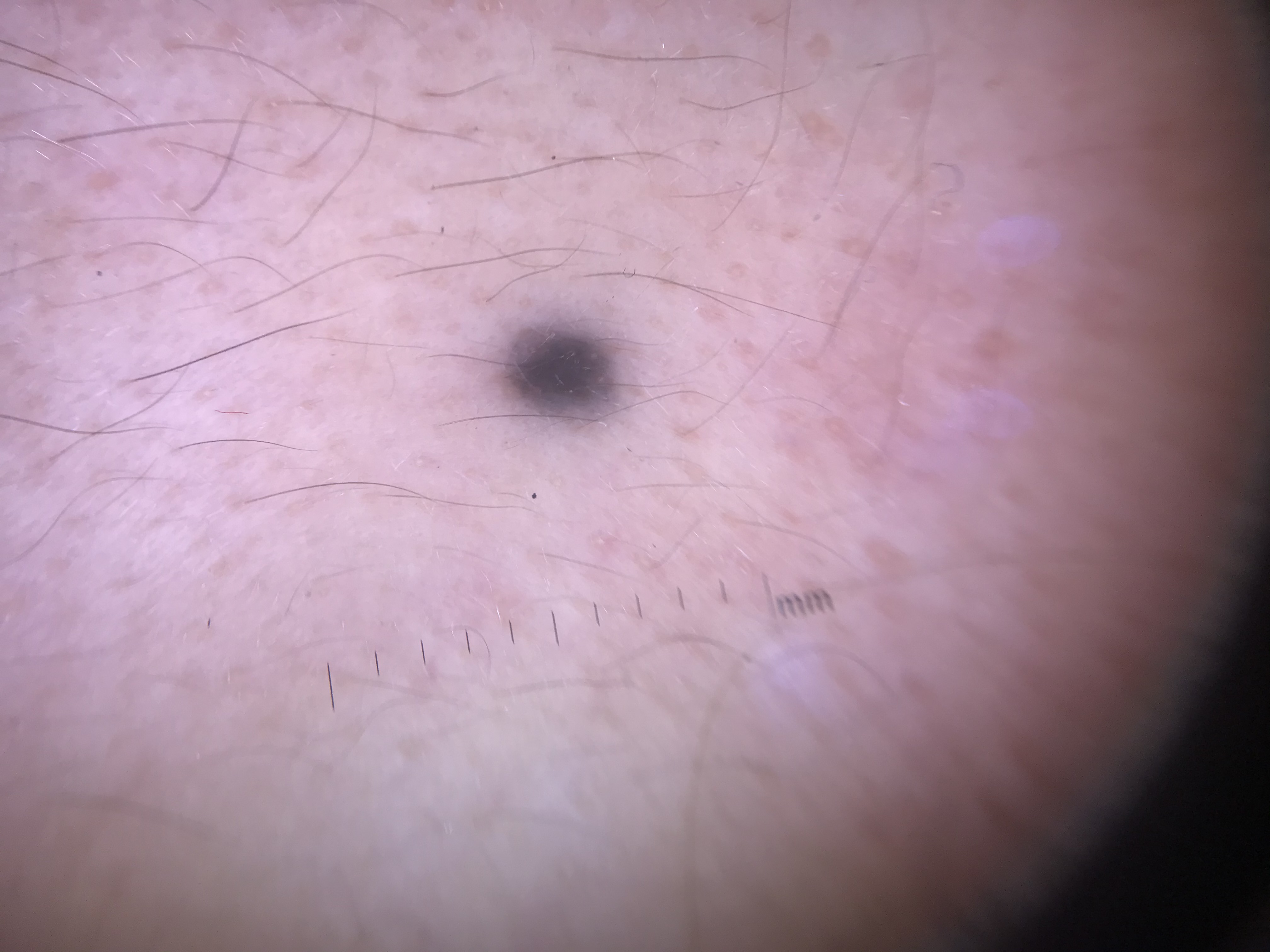Case:
- label · blue nevus (expert consensus)